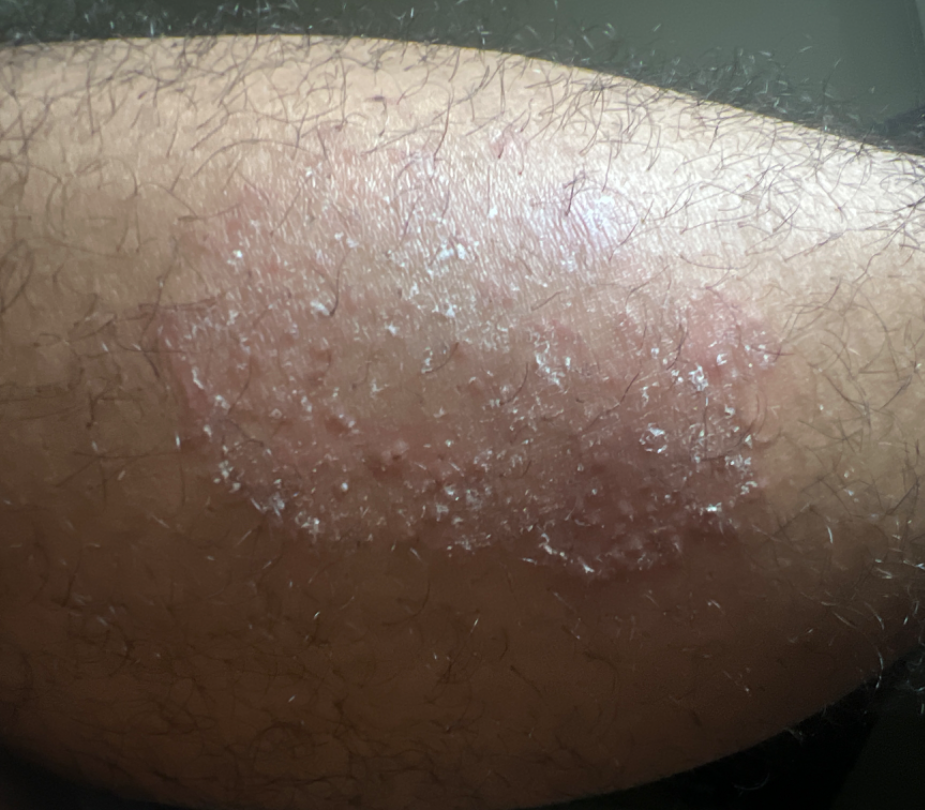Single-reviewer assessment: the impression is Tinea.